Female contributor, age 40–49. The condition has been present for less than one week. The lesion is associated with darkening, pain, burning and bothersome appearance. The patient indicates associated mouth sores. The patient indicates the lesion is flat. The lesion involves the back of the hand. The photo was captured at an angle — 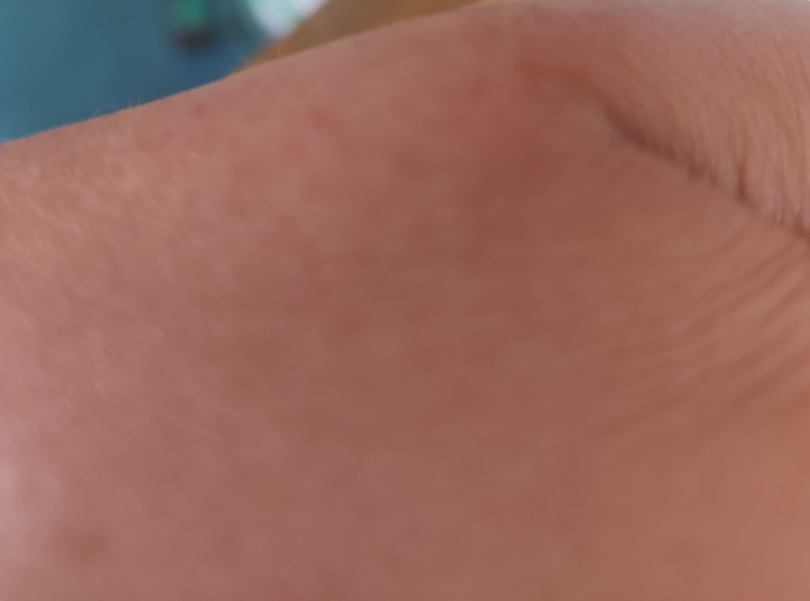<report>
  <differential>
    <leading>Eczema</leading>
    <considered>Irritant Contact Dermatitis</considered>
    <unlikely>Allergic Contact Dermatitis</unlikely>
  </differential>
</report>